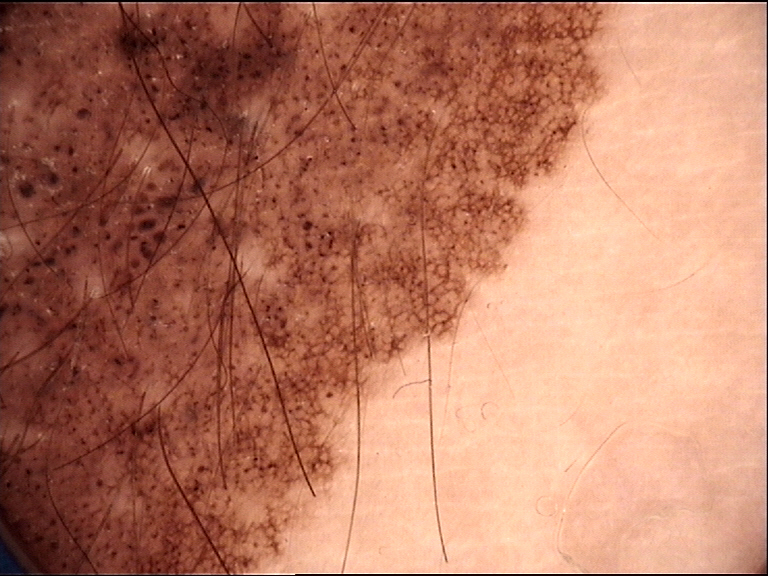classification = banal
assessment = congenital compound nevus (expert consensus)